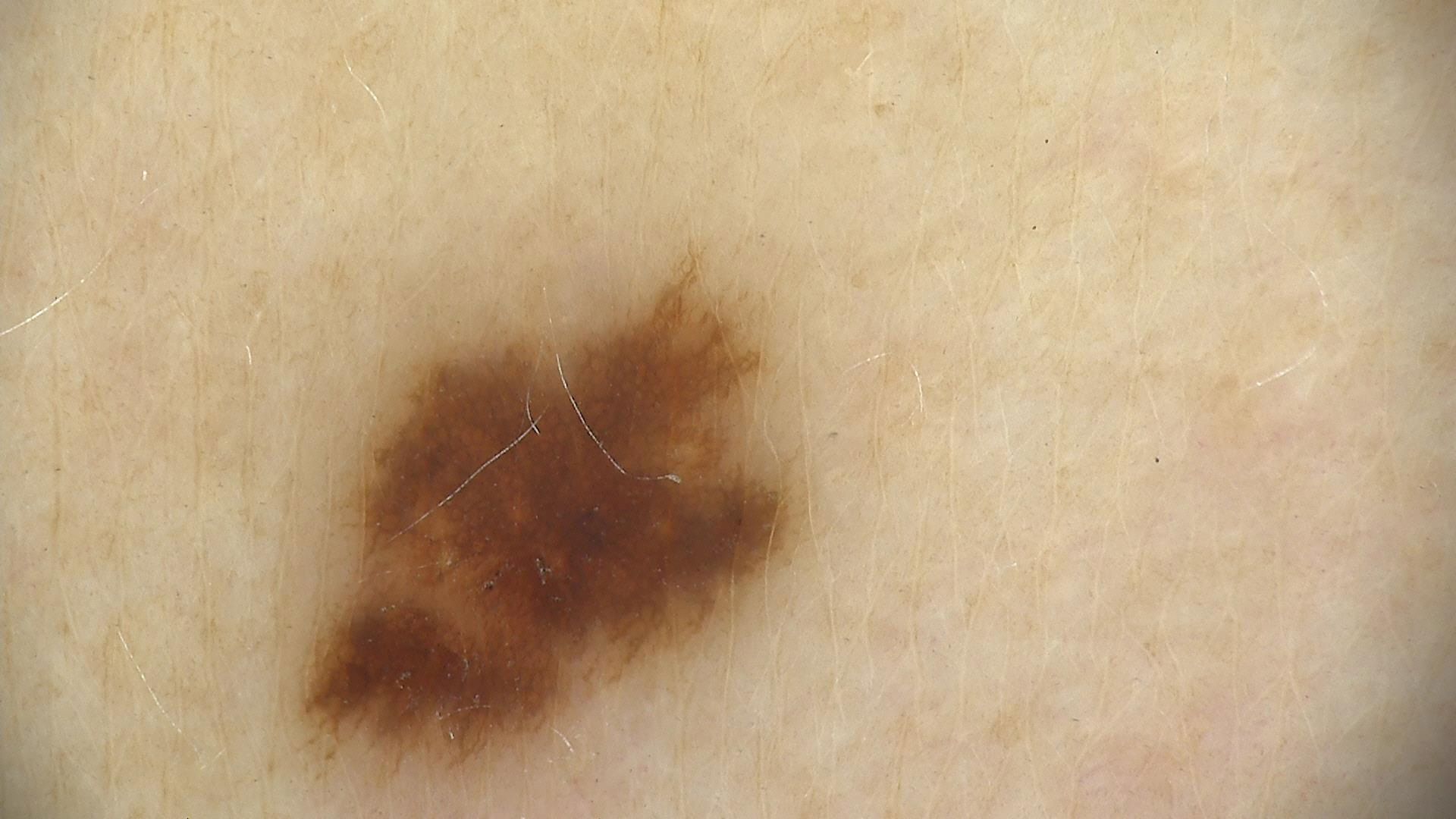A dermoscopic close-up of a skin lesion.
The diagnosis was a benign lesion — a dysplastic junctional nevus.